The leg is involved · close-up view · the patient is a male aged 40–49.
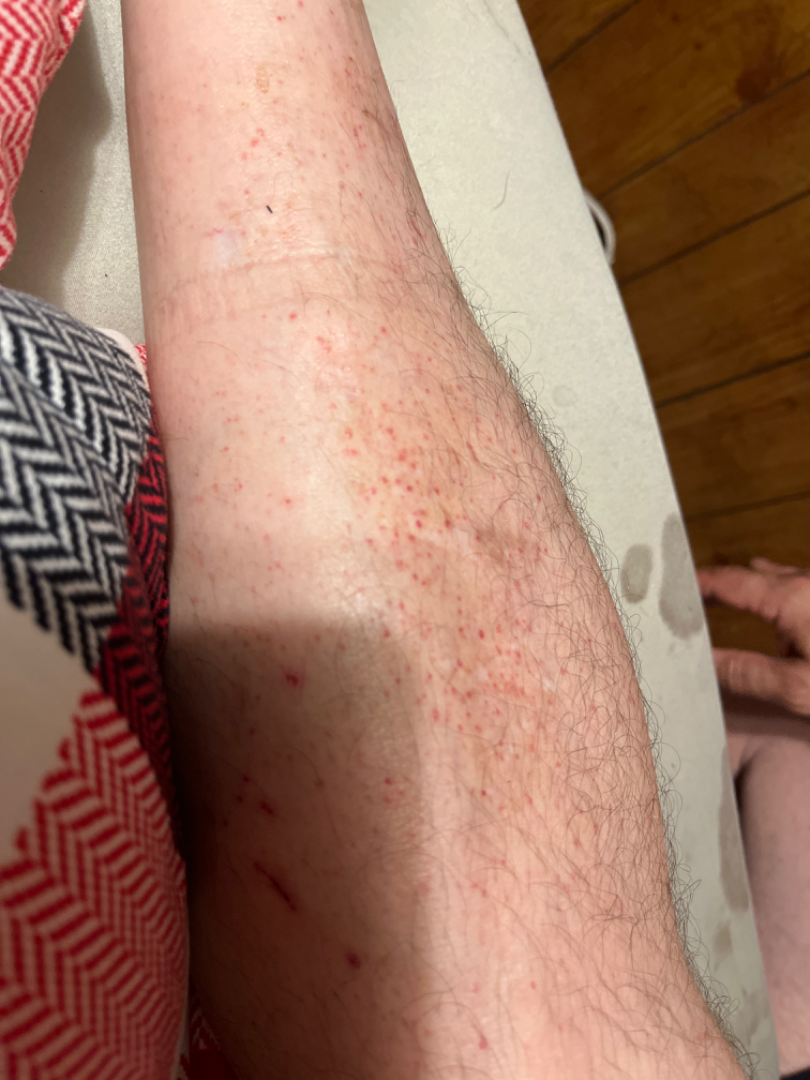history = one to four weeks
self-categorized as = skin that appeared healthy to them
described texture = flat
assessment = Pigmented purpuric eruption (considered); Leukocytoclastic Vasculitis (considered)